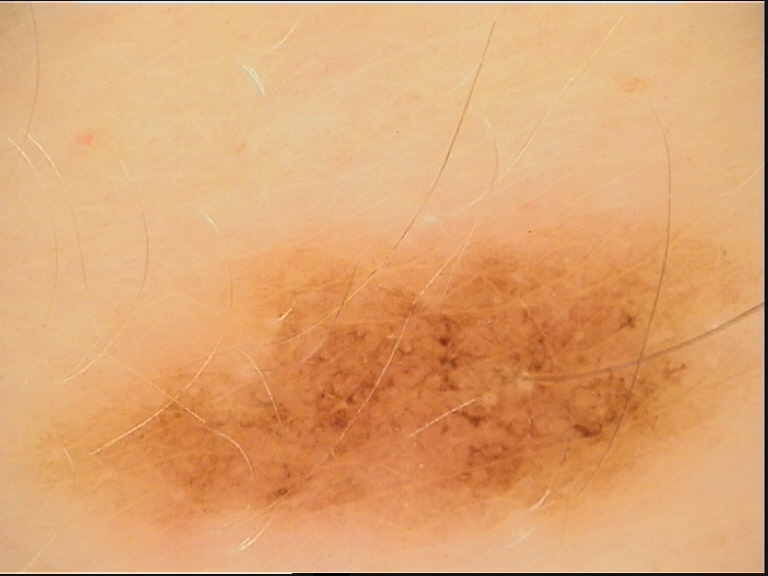Findings:
- assessment · dysplastic junctional nevus (expert consensus)